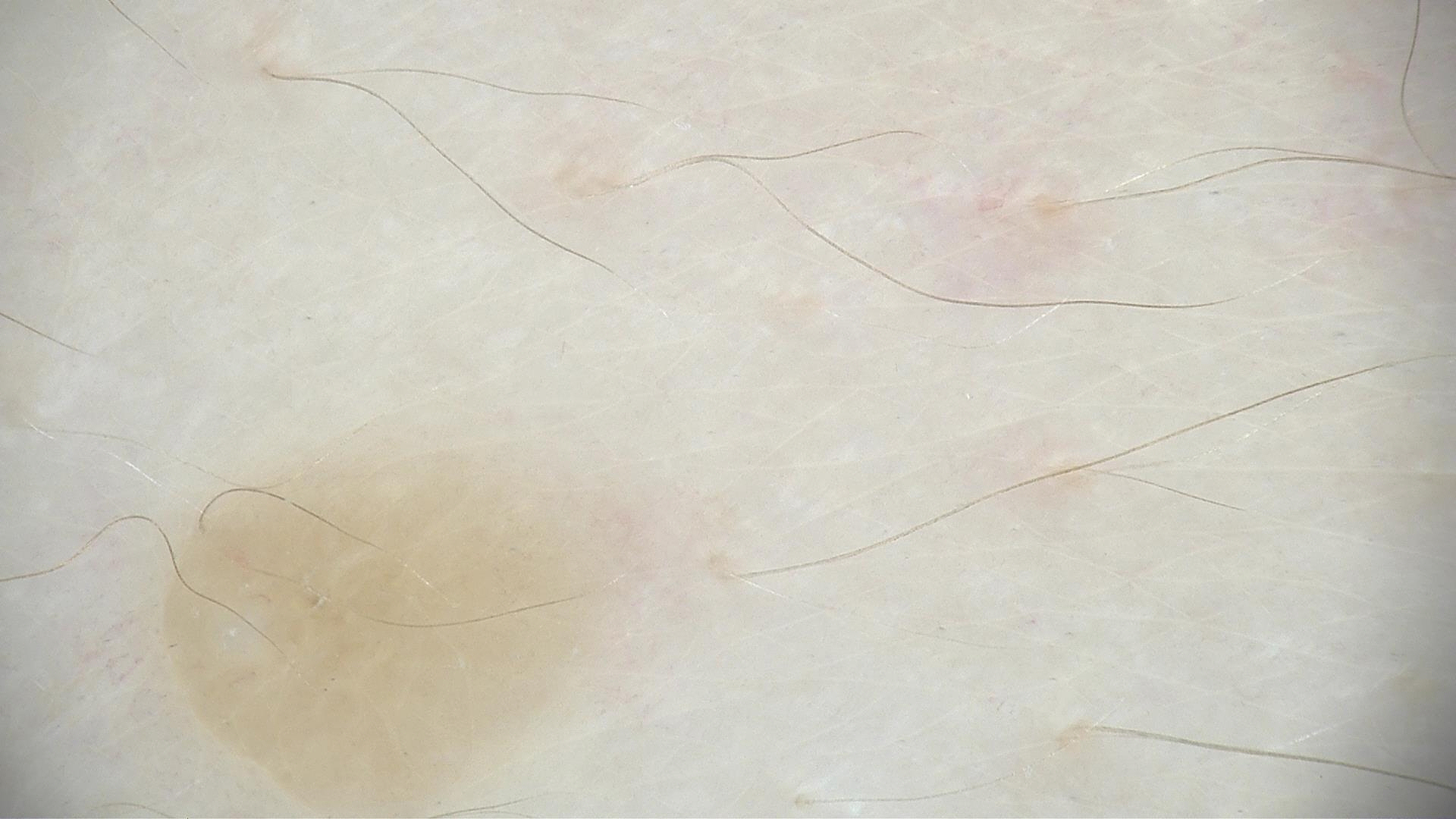assessment = dermal nevus (expert consensus).